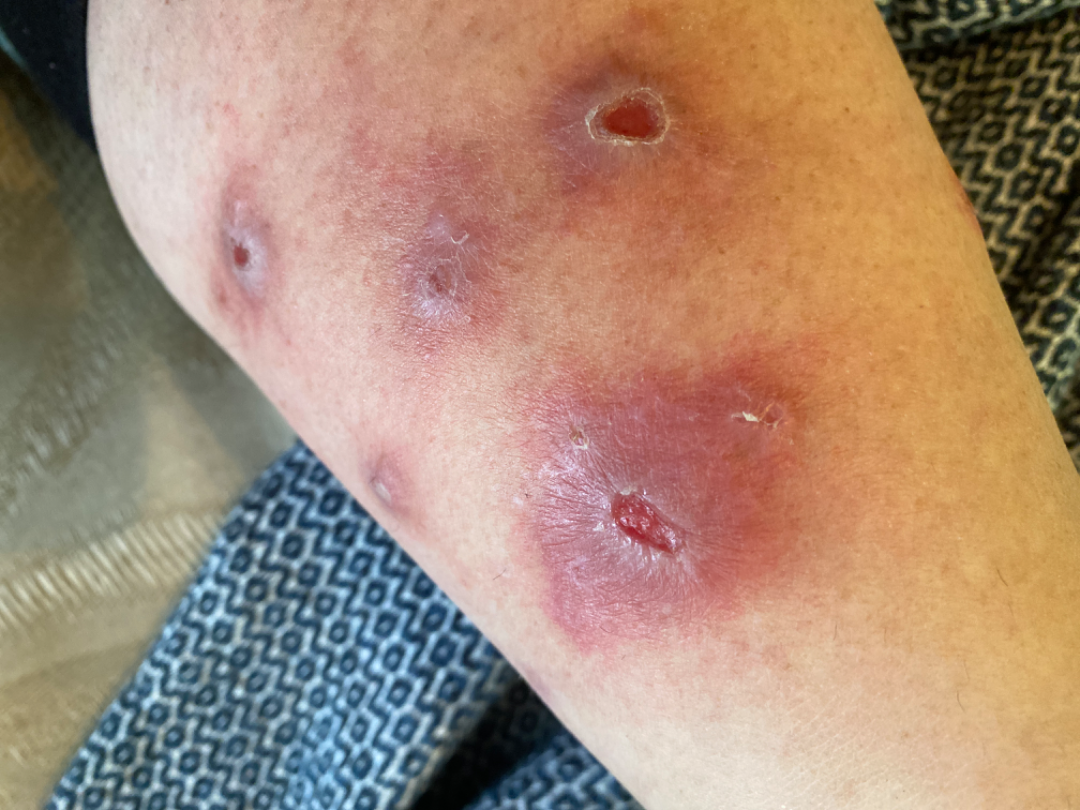assessment: indeterminate from the photograph | skin tone: FST IV; lay graders estimated MST 2 or 3 | reported symptoms: enlargement and bothersome appearance | systemic symptoms: joint pain, fatigue and shortness of breath | subject: female, age 40–49 | body site: leg | framing: at an angle.